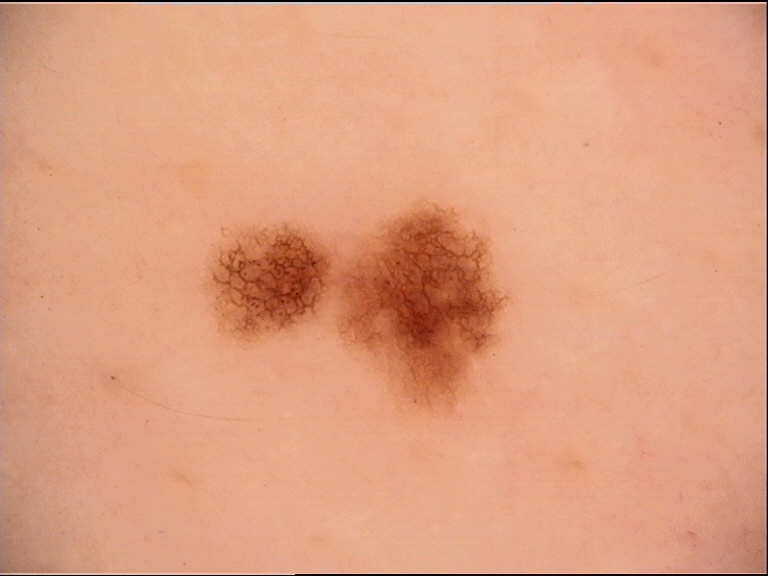{
  "diagnosis": {
    "name": "dysplastic junctional nevus",
    "code": "jd",
    "malignancy": "benign",
    "super_class": "melanocytic",
    "confirmation": "expert consensus"
  }
}